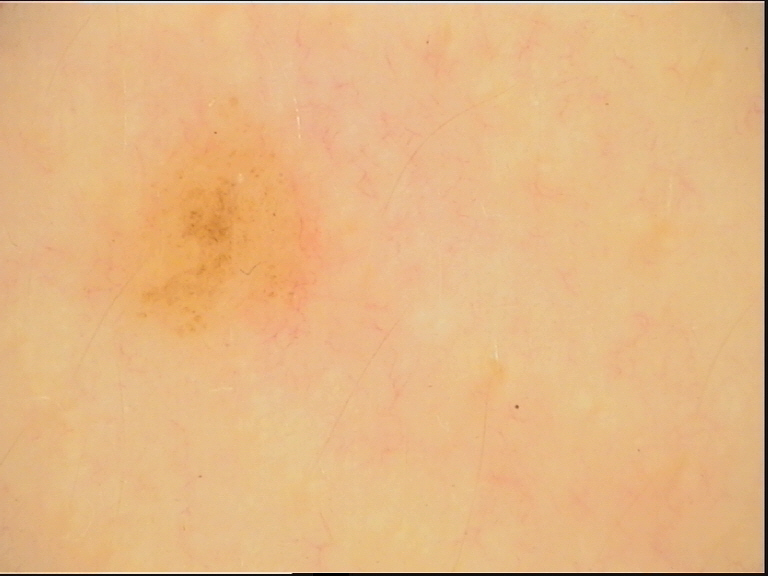A dermoscopic close-up of a skin lesion. Classified as a dysplastic junctional nevus.